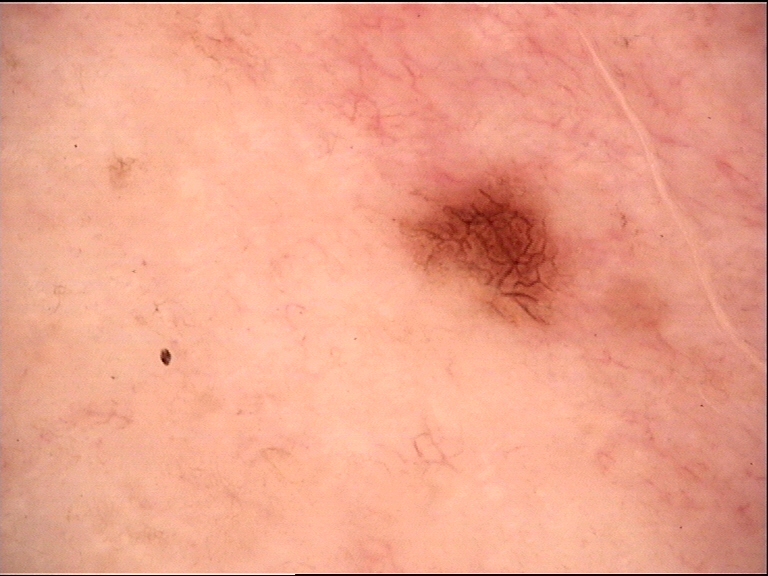| field | value |
|---|---|
| image type | dermoscopy |
| assessment | dysplastic junctional nevus (expert consensus) |